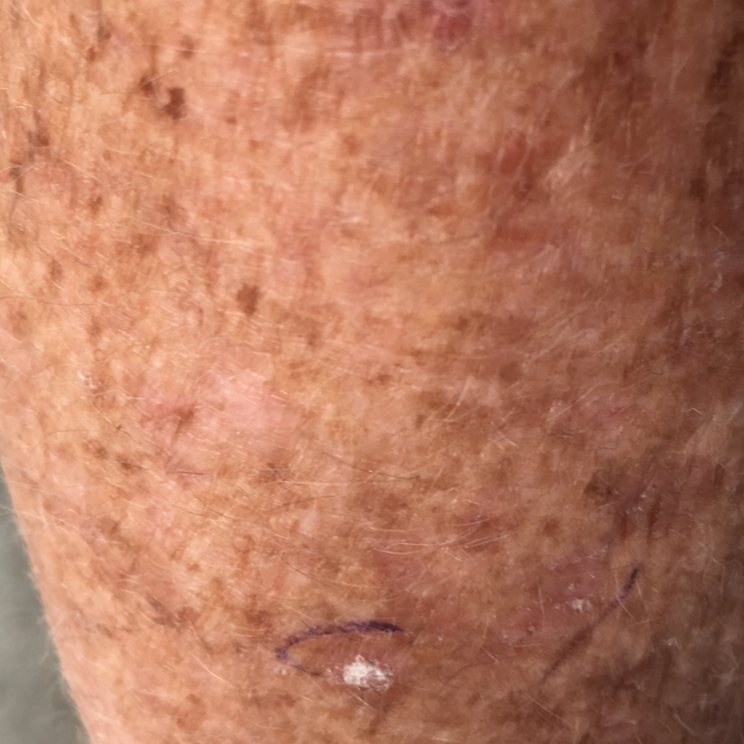By history, prior malignancy (patient or family).
A clinical photograph of a skin lesion.
Located on an arm.
The lesion measures 4 × 4 mm.
The patient reports that the lesion itches.
The diagnostic impression was a premalignant lesion — an actinic keratosis.